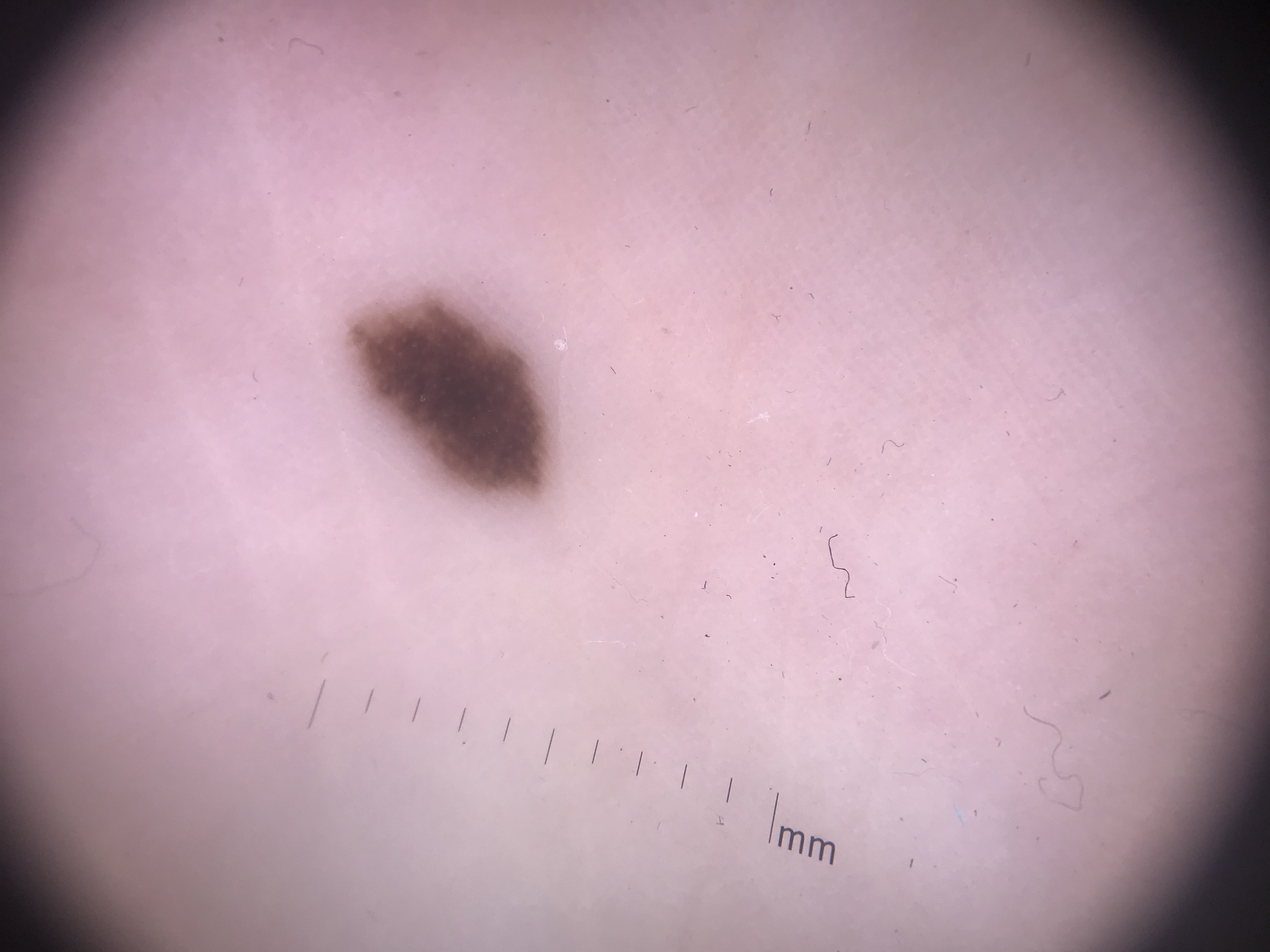diagnostic label: acral junctional nevus (expert consensus).